The patient indicates the lesion is raised or bumpy · the photo was captured at a distance · no constitutional symptoms were reported · the leg and arm are involved · Fitzpatrick skin type V — 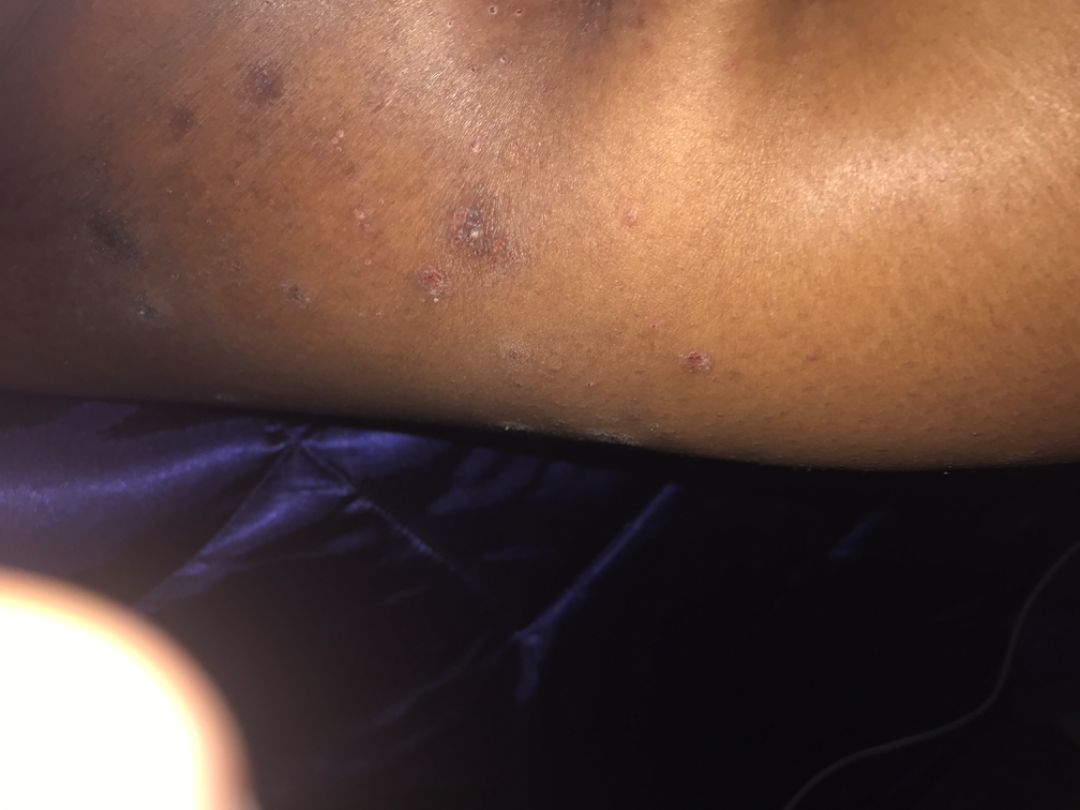The impression on review was Eczema.